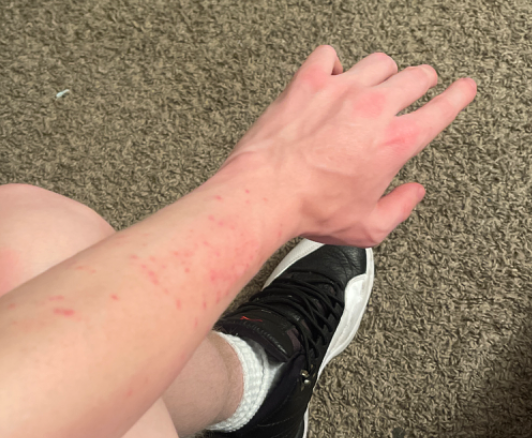Review:
The favored diagnosis is Insect Bite; the differential also includes Eczema; an alternative is Scabies.